A skin lesion imaged with a dermatoscope.
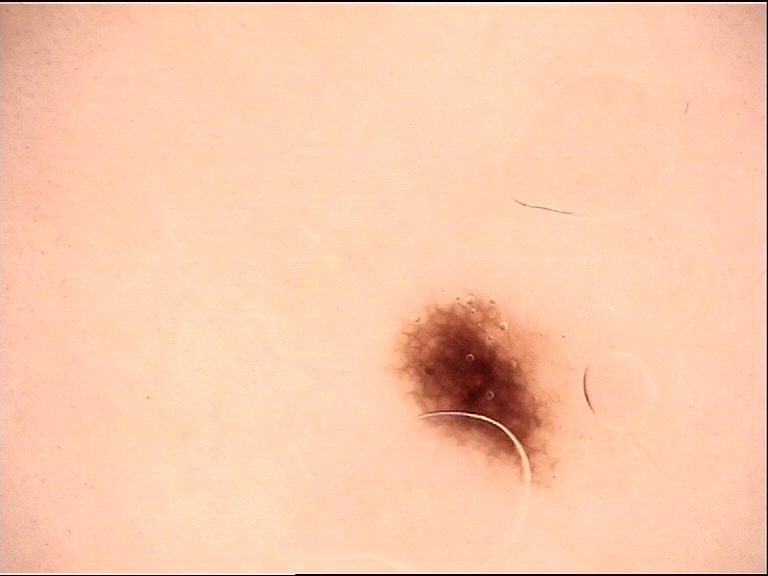Impression: Diagnosed as a benign lesion — a dysplastic junctional nevus.